A dermoscopic close-up of a skin lesion:
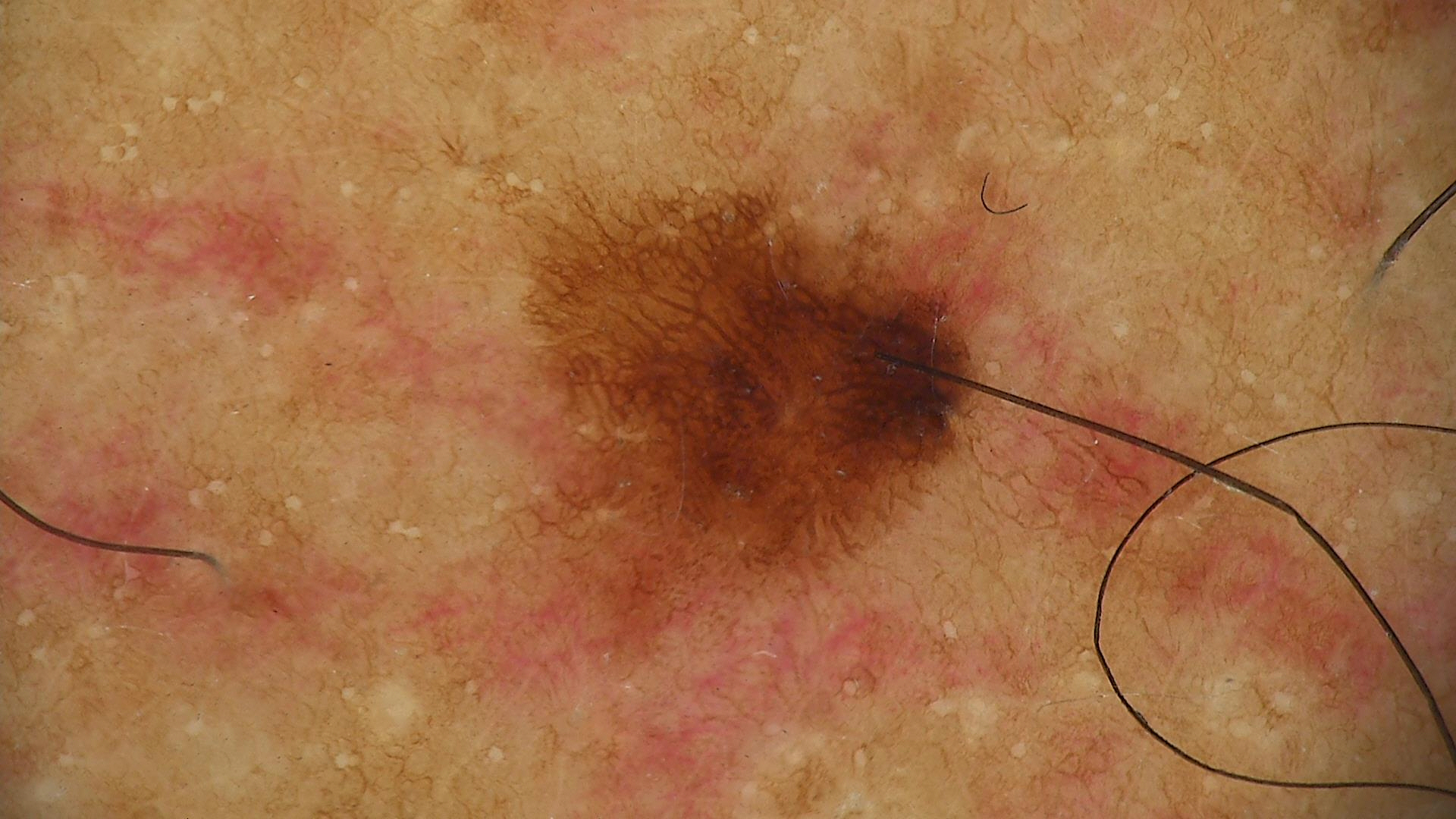Consistent with a dysplastic junctional nevus.